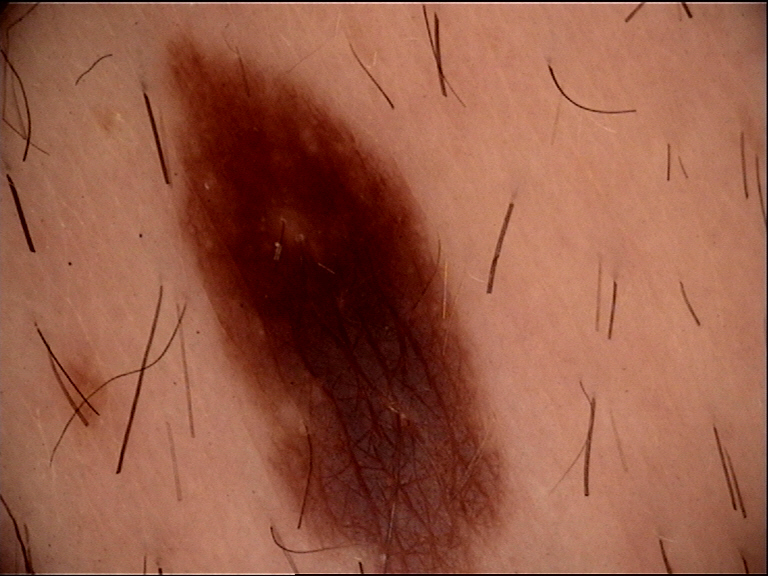modality: dermatoscopy
diagnostic label: dysplastic junctional nevus (expert consensus)